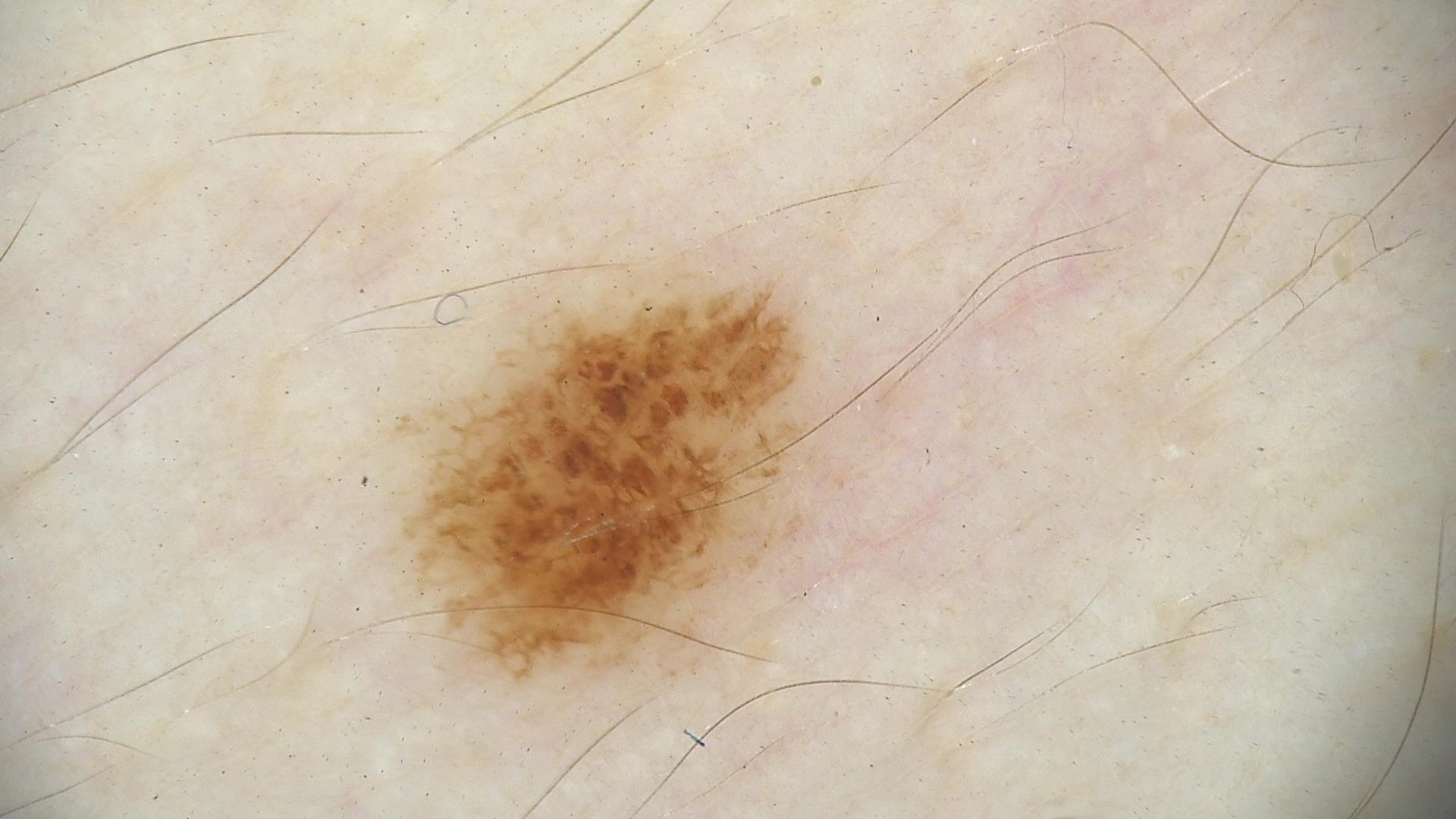A dermoscopic close-up of a skin lesion. The diagnosis was a dysplastic junctional nevus.